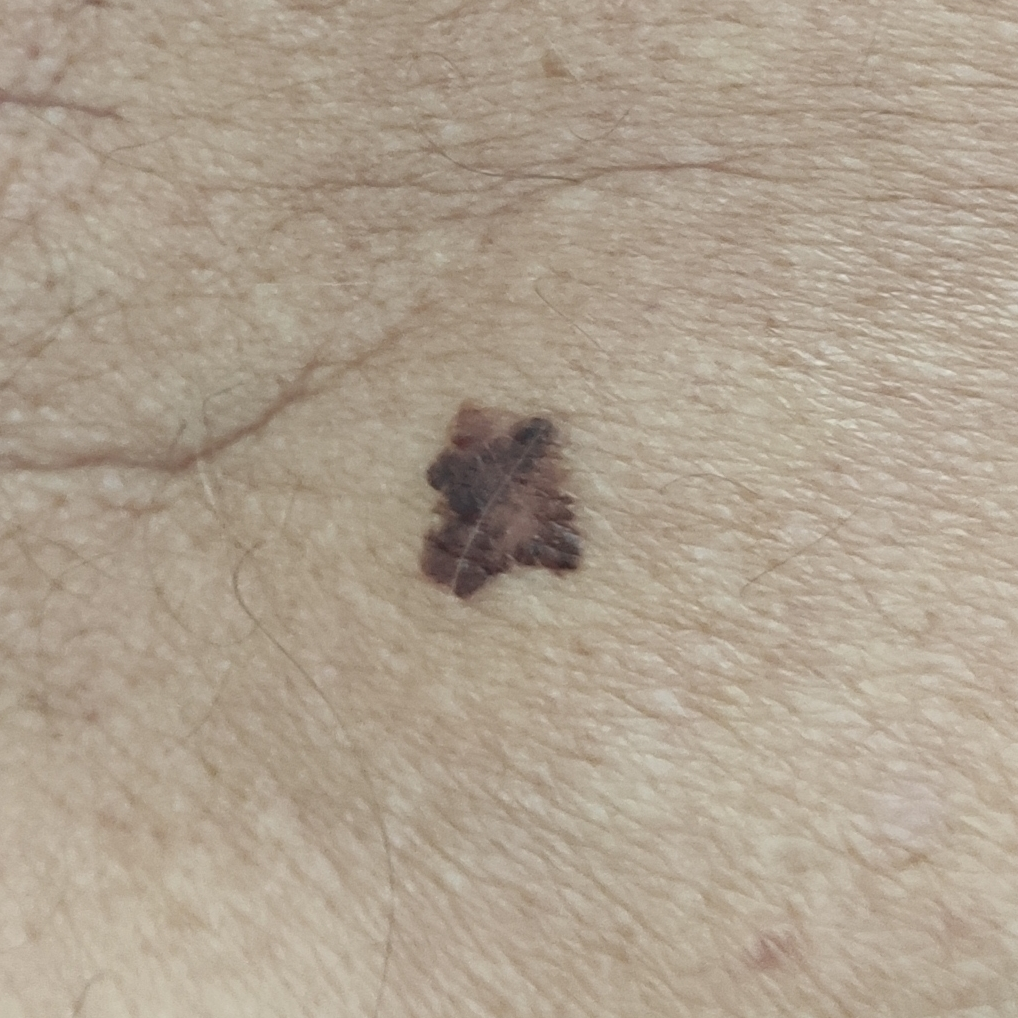History notes prior malignancy (patient or family), prior skin cancer (patient or family), and tobacco use. FST II. A male subject 78 years of age. A smartphone photograph of a skin lesion. The lesion is on the back. The lesion measures 10 × 10 mm. Per patient report, the lesion has changed, is elevated, and has grown, but has not bled and does not hurt. The biopsy diagnosis was a melanoma.